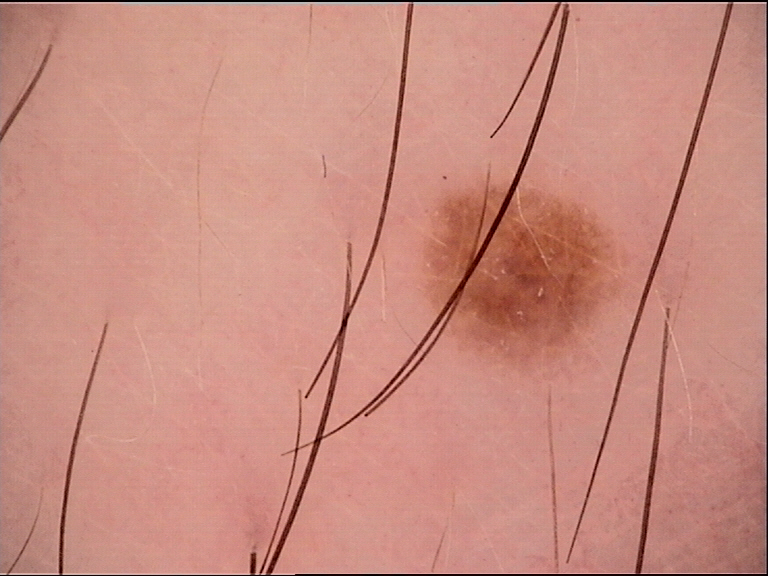imaging: dermoscopy; lesion type: banal; diagnostic label: junctional nevus (expert consensus).